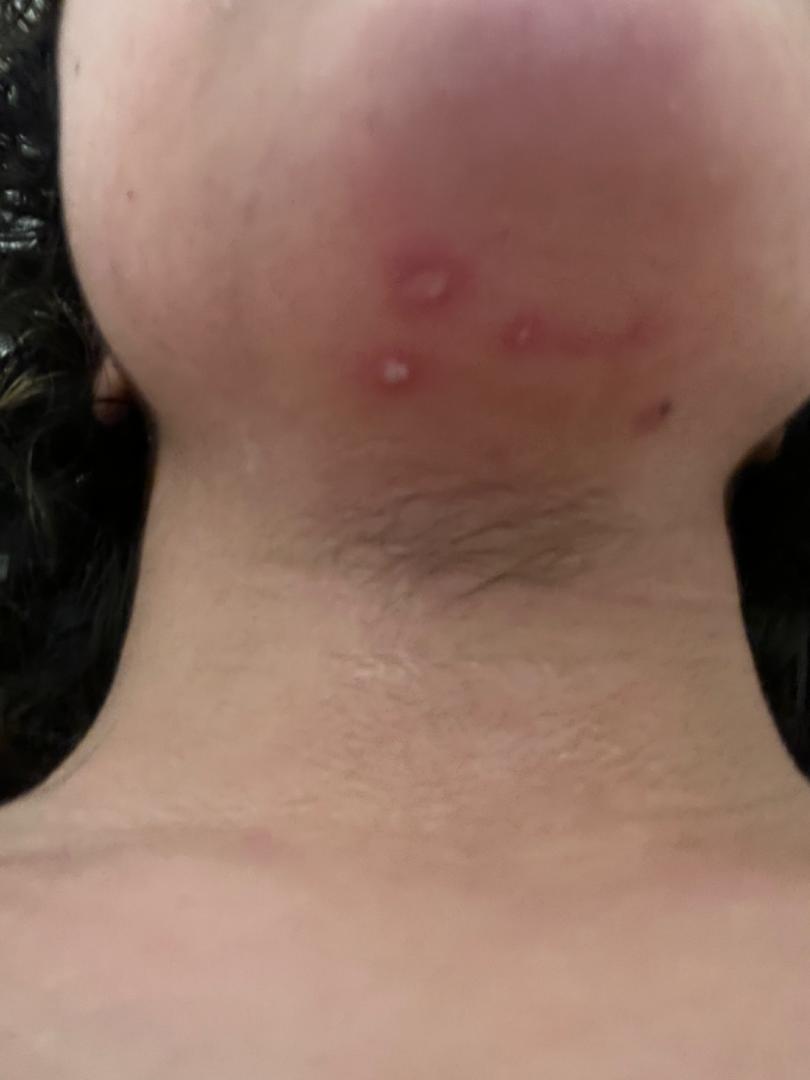Skin tone: Fitzpatrick III. Present for less than one week. Reported lesion symptoms include bothersome appearance, burning, bleeding, pain and itching. The contributor notes the lesion is raised or bumpy and fluid-filled. An image taken at an angle. Located on the head or neck. Impetigo (leading); Folliculitis (possible).